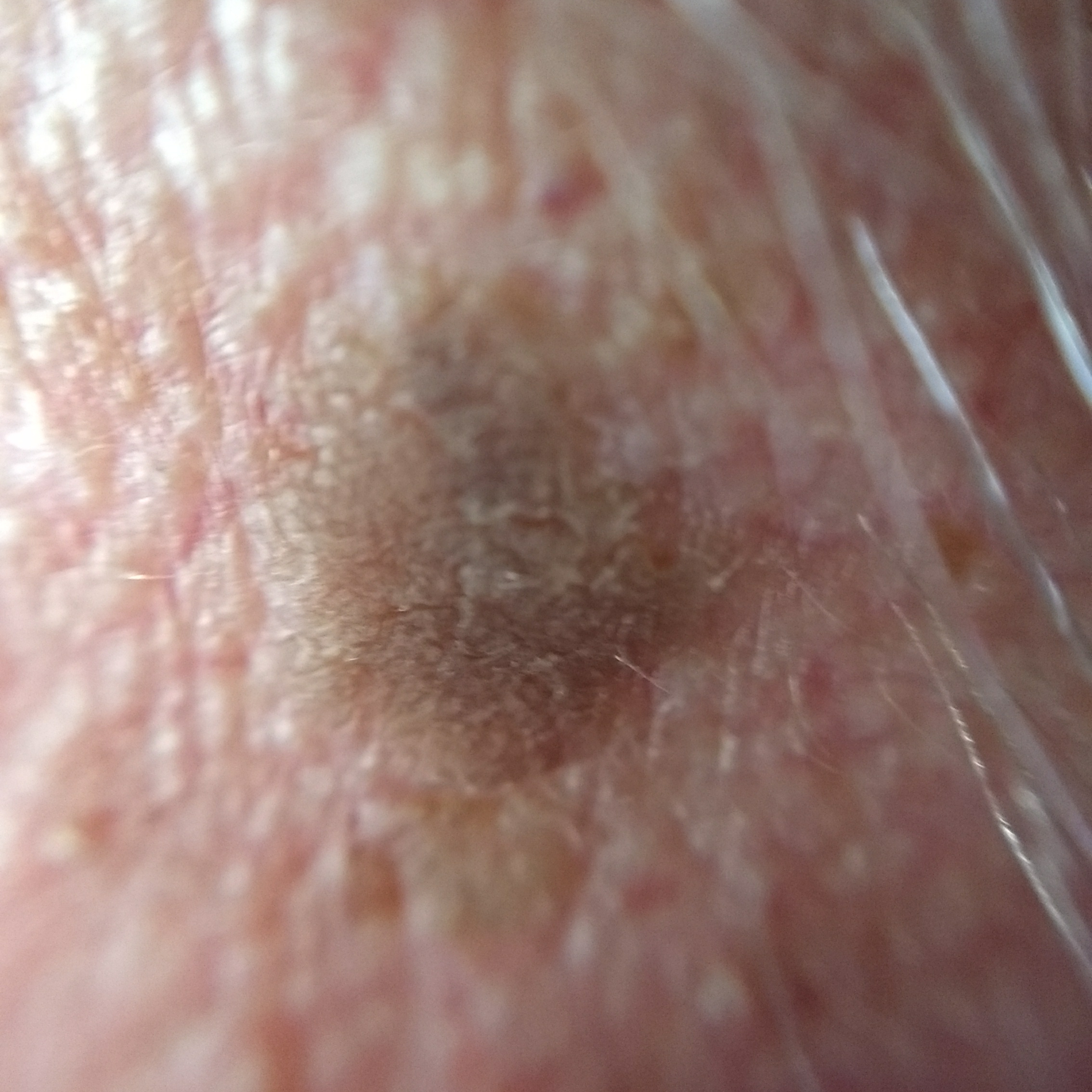- subject · 69 years of age
- image type · smartphone clinical photo
- body site · the face
- reported symptoms · elevation / no pain, no growth
- diagnostic label · seborrheic keratosis (clinical consensus)